A dermoscopic image of a skin lesion · the subject is a female aged 68 to 72:
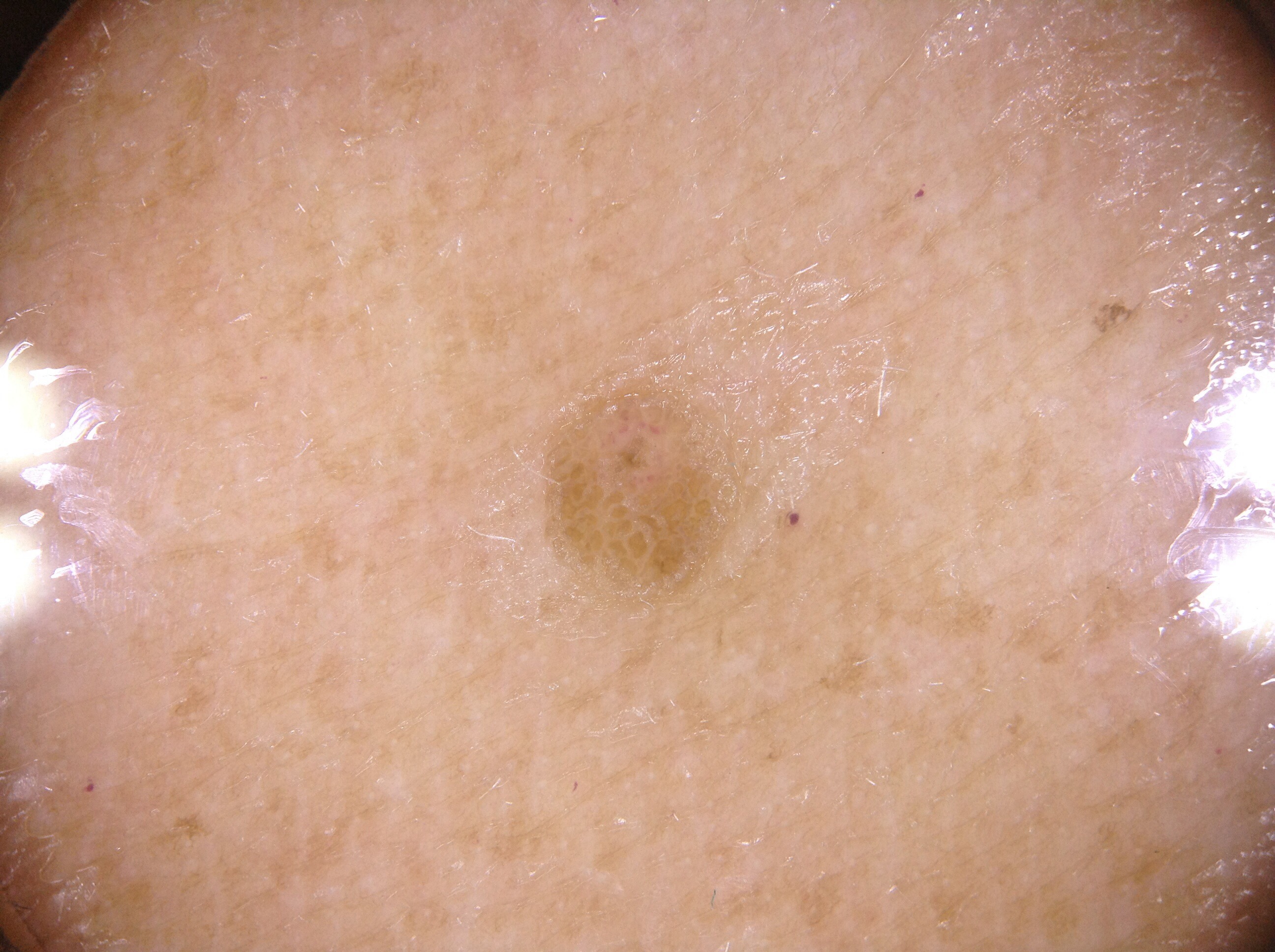Dermoscopy demonstrates negative network. In (x1, y1, x2, y2) order, the lesion's extent is bbox(544, 376, 740, 615). A small lesion within a wider field of skin. The diagnostic assessment was a seborrheic keratosis, a benign lesion.